By history, prior malignancy (patient or family), pesticide exposure, prior skin cancer (patient or family), and no tobacco use · a smartphone photograph of a skin lesion · the patient was assessed as Fitzpatrick I: 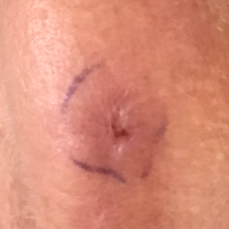The lesion involves the face. The patient describes that the lesion itches, hurts, has bled, and is elevated. The biopsy diagnosis was an actinic keratosis.